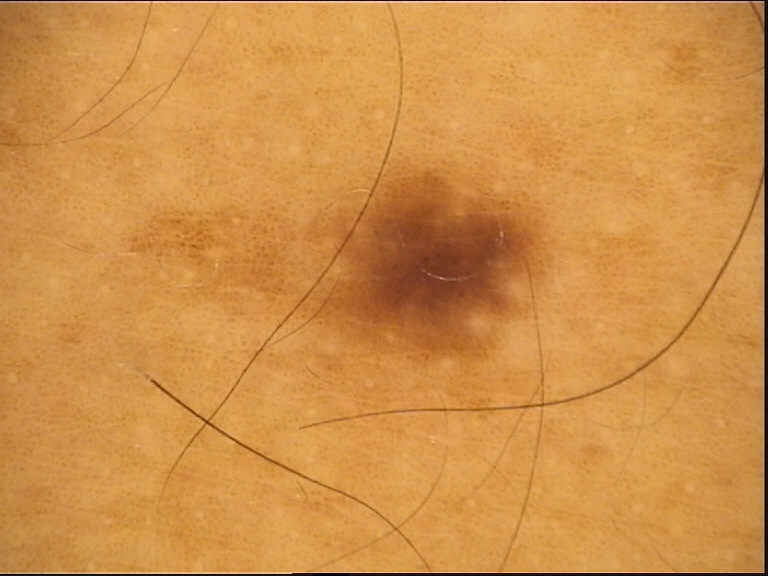Labeled as a dysplastic junctional nevus.